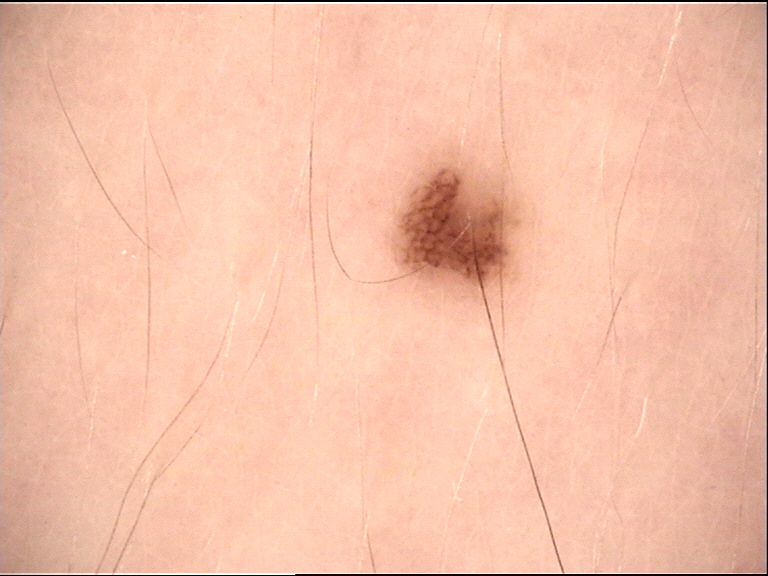Case:
A dermoscopic photograph of a skin lesion.
Conclusion:
The diagnosis was a dysplastic junctional nevus.